An image taken at a distance: 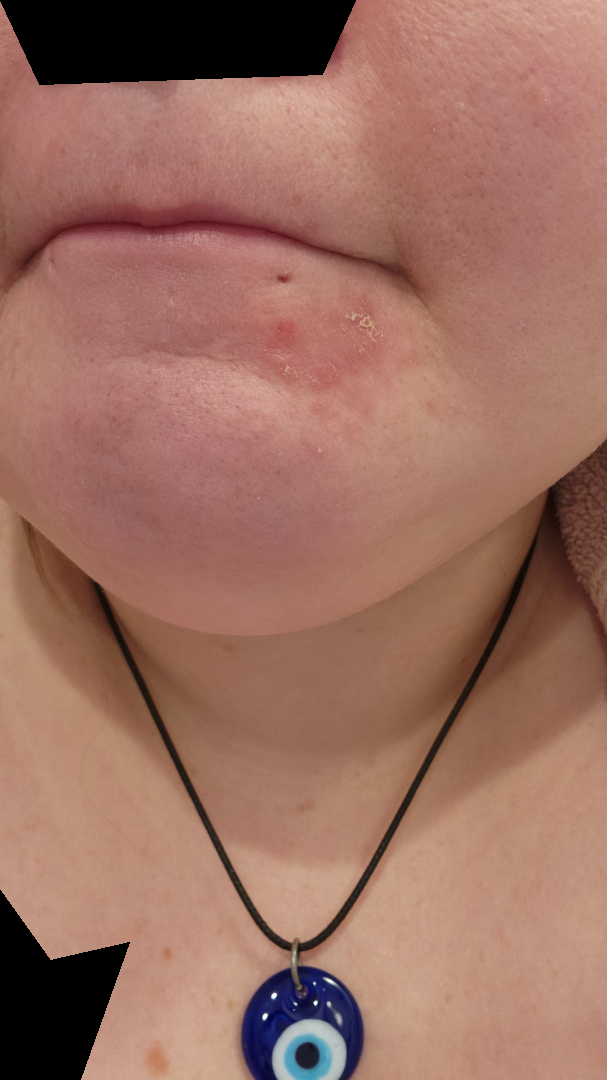diagnostic considerations: favoring Perioral Dermatitis; also consider Impetigo; possibly Irritant Contact Dermatitis